A close-up photograph; the lesion involves the front of the torso; the subject is a male aged 40–49.
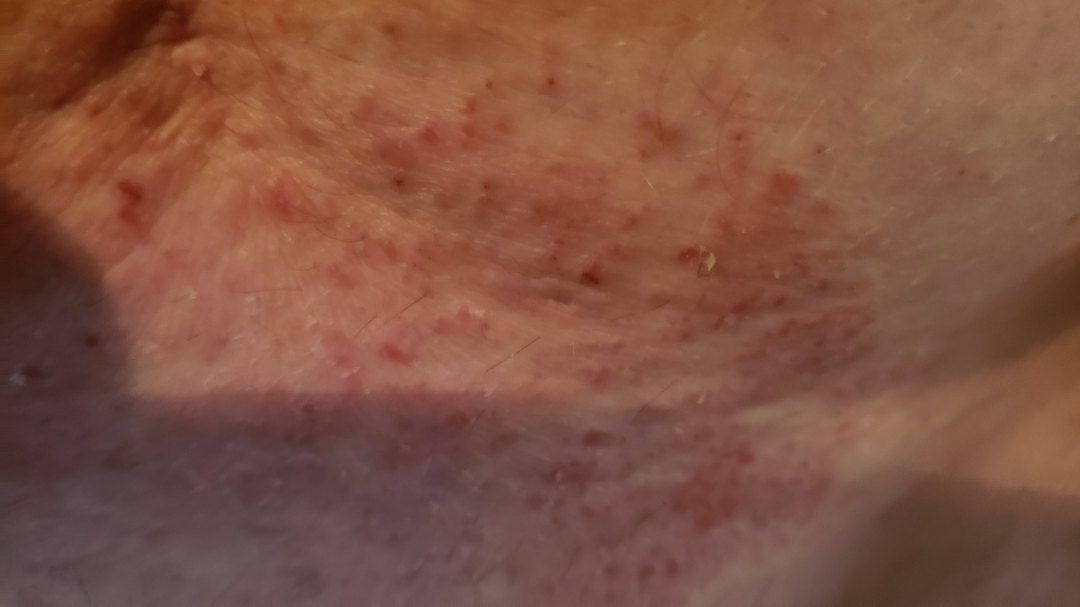Notes:
– described texture · raised or bumpy and rough or flaky
– lesion symptoms · itching, burning, pain and enlargement
– present for · three to twelve months
– associated systemic symptoms · none reported
– differential diagnosis · the impression on review was Lichenified eczematous dermatitis